The photograph was taken at an angle; the lesion involves the leg and arm: 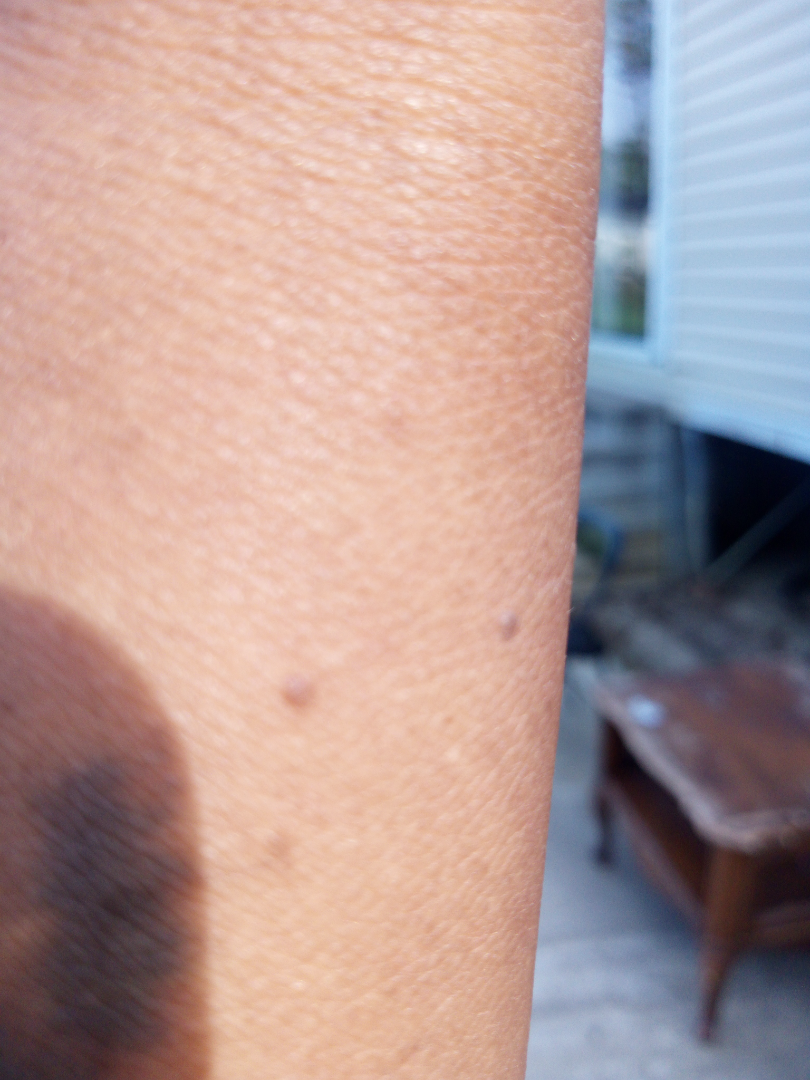| field | value |
|---|---|
| assessment | not assessable |
| surface texture | flat and raised or bumpy |
| patient-reported symptoms | pain, itching, bothersome appearance, enlargement, darkening and burning |
| present for | one to three months |